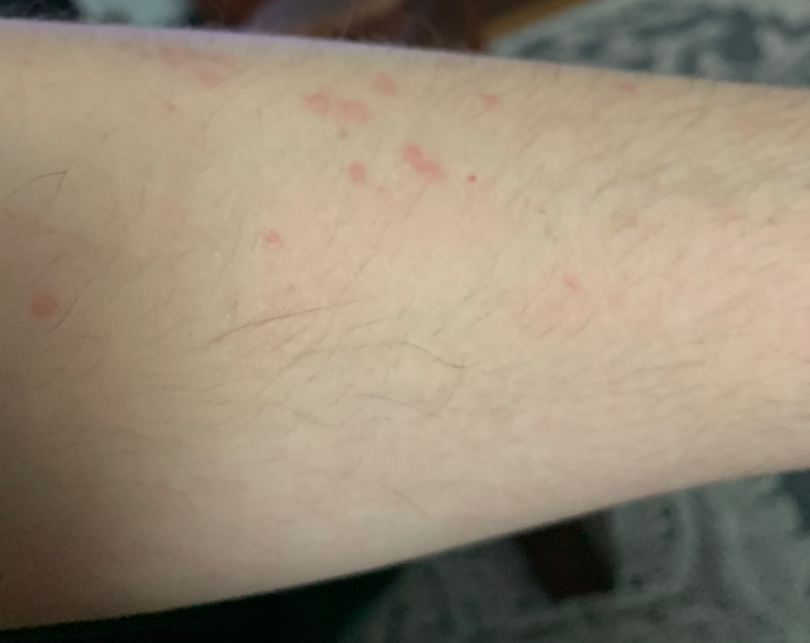assessment: ungradable on photographic review; location: arm, head or neck and leg; lesion symptoms: itching and enlargement; framing: at an angle; self-categorized as: a rash.